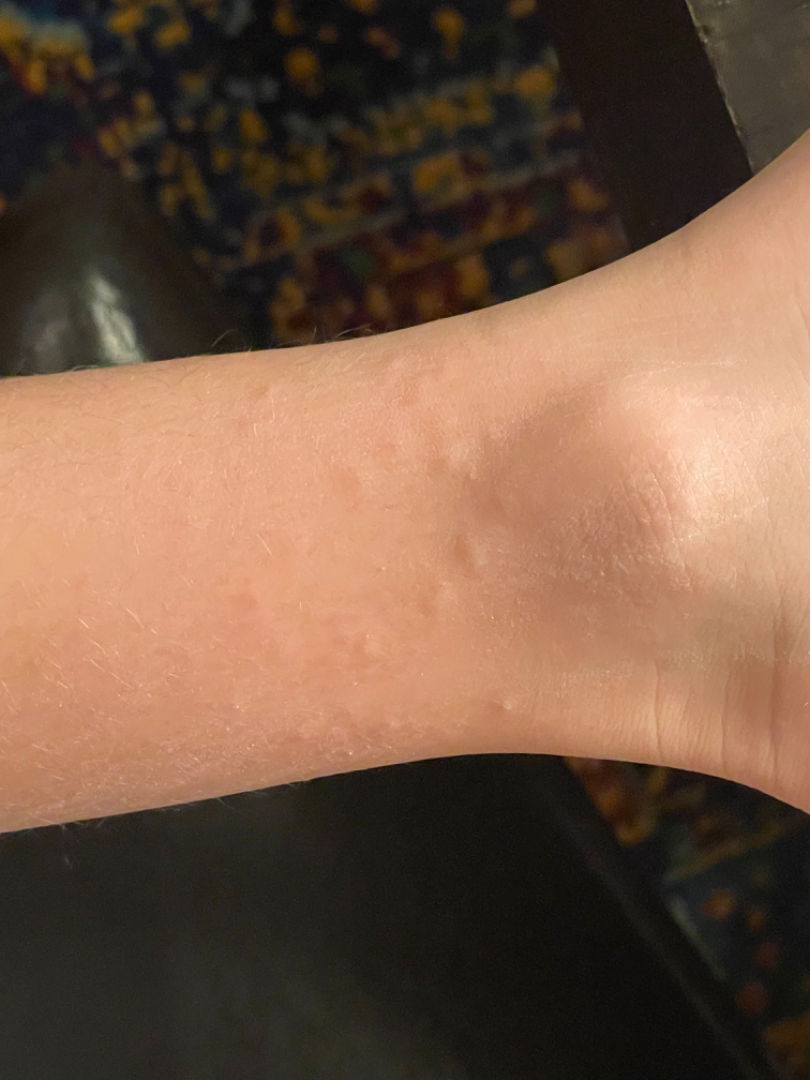view: close-up, body site: leg, skin tone: FST II; lay reviewers estimated Monk Skin Tone 4 (US pool) or 3 (India pool), history: about one day.